The affected area is the leg · an image taken at an angle · the contributor is a female aged 40–49: 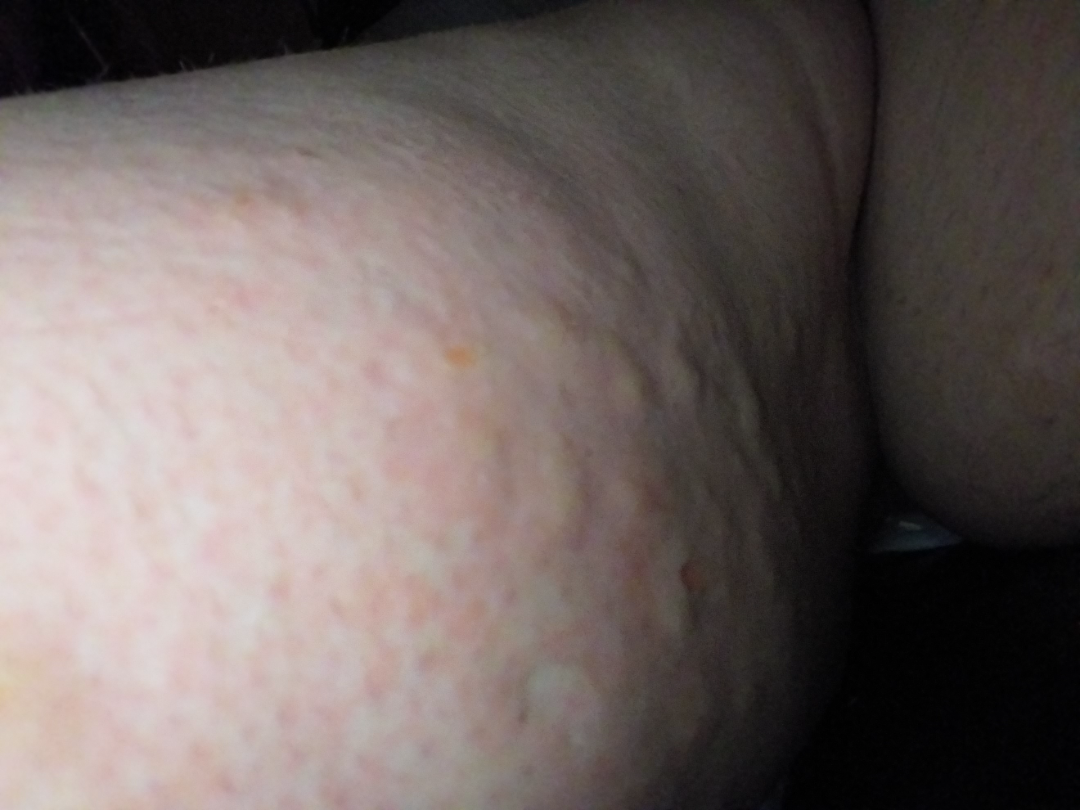Symptoms reported: itching, bleeding and enlargement. The patient described the issue as a rash. Reported duration is one to four weeks. The patient reports the lesion is raised or bumpy, fluid-filled and rough or flaky. The reviewing panel's impression was: Urticaria and Allergic Contact Dermatitis were considered with similar weight.